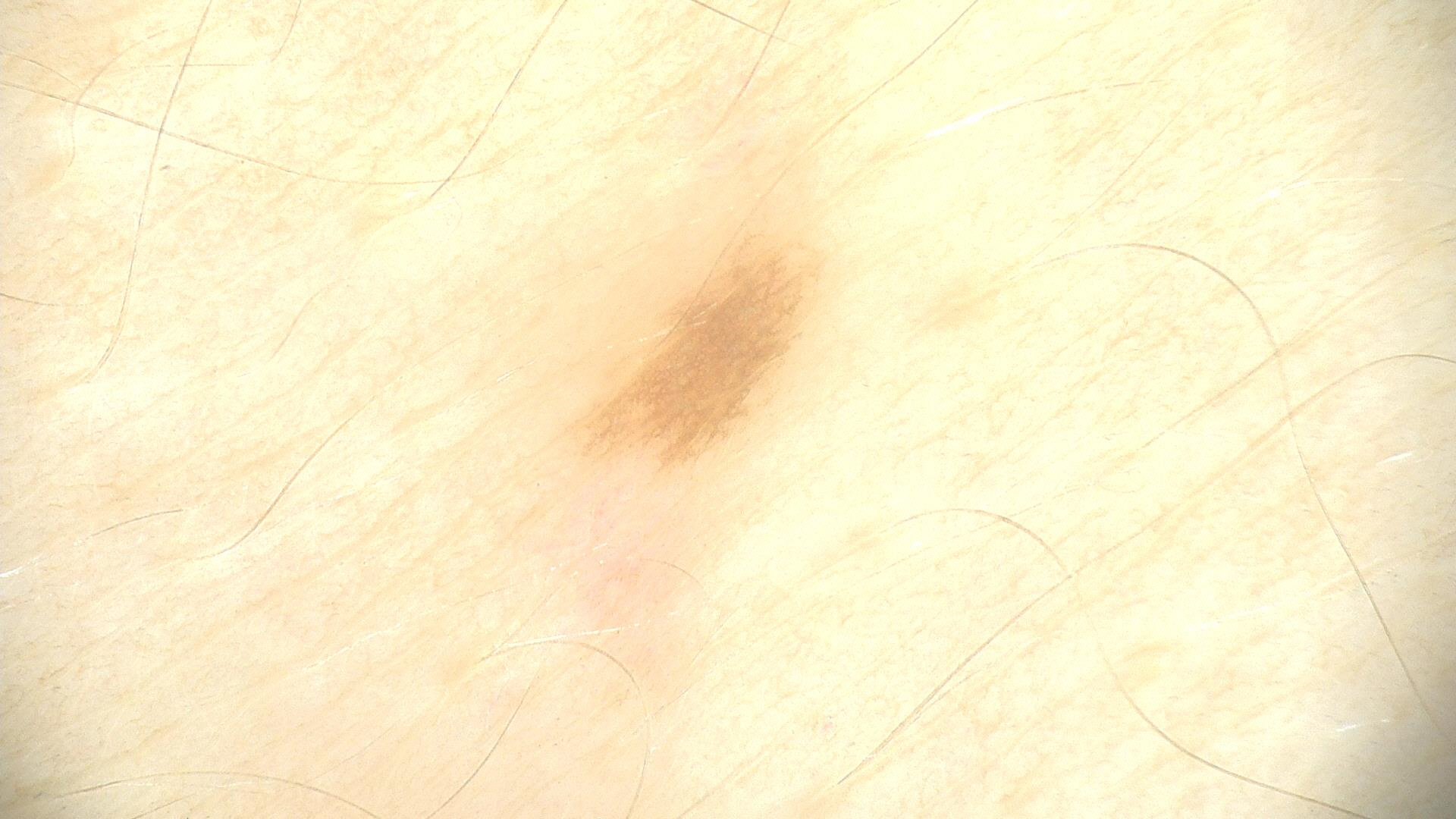Conclusion:
Consistent with an acral dysplastic junctional nevus.